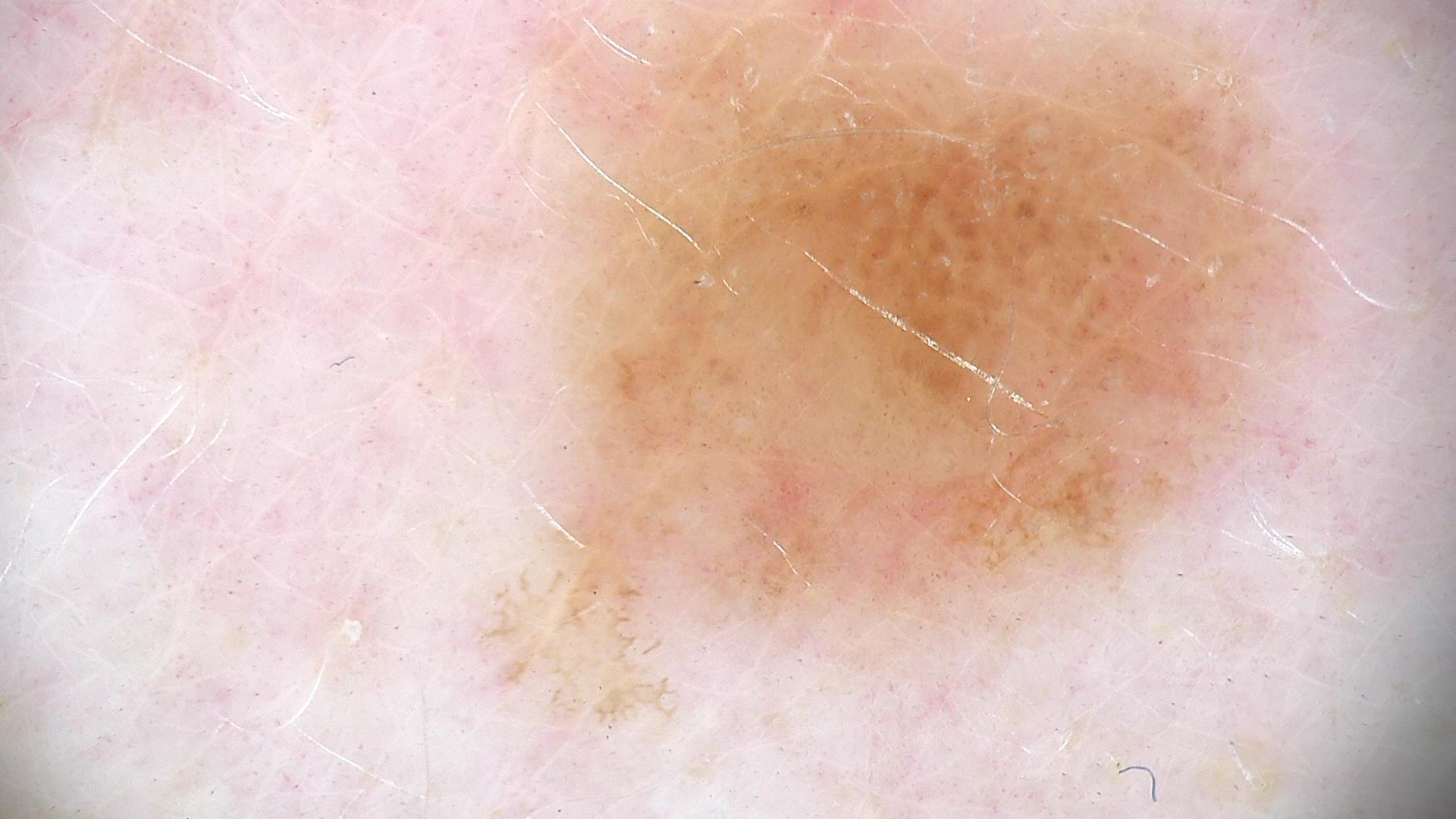A dermoscopy image of a single skin lesion.
Diagnosed as a dysplastic junctional nevus.